Dermoscopy of a skin lesion: 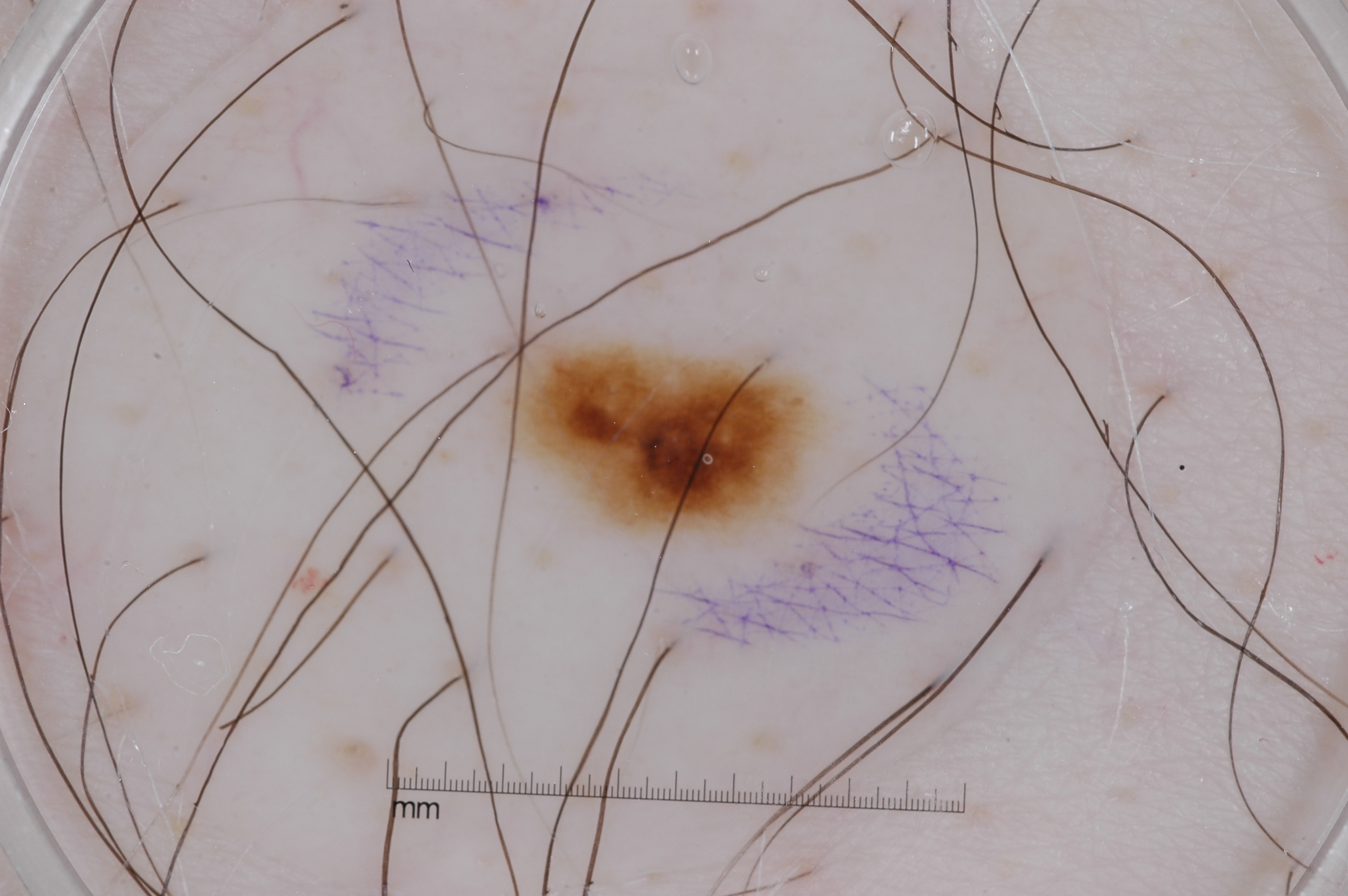Image and clinical context:
As (left, top, right, bottom), the lesion is located at 506/343/811/532. The dermoscopic pattern shows no pigment network, streaks, negative network, or milia-like cysts. The lesion covers approximately 4% of the dermoscopic field.
Conclusion:
Expert review diagnosed this as a melanocytic nevus.